This image was taken at a distance.
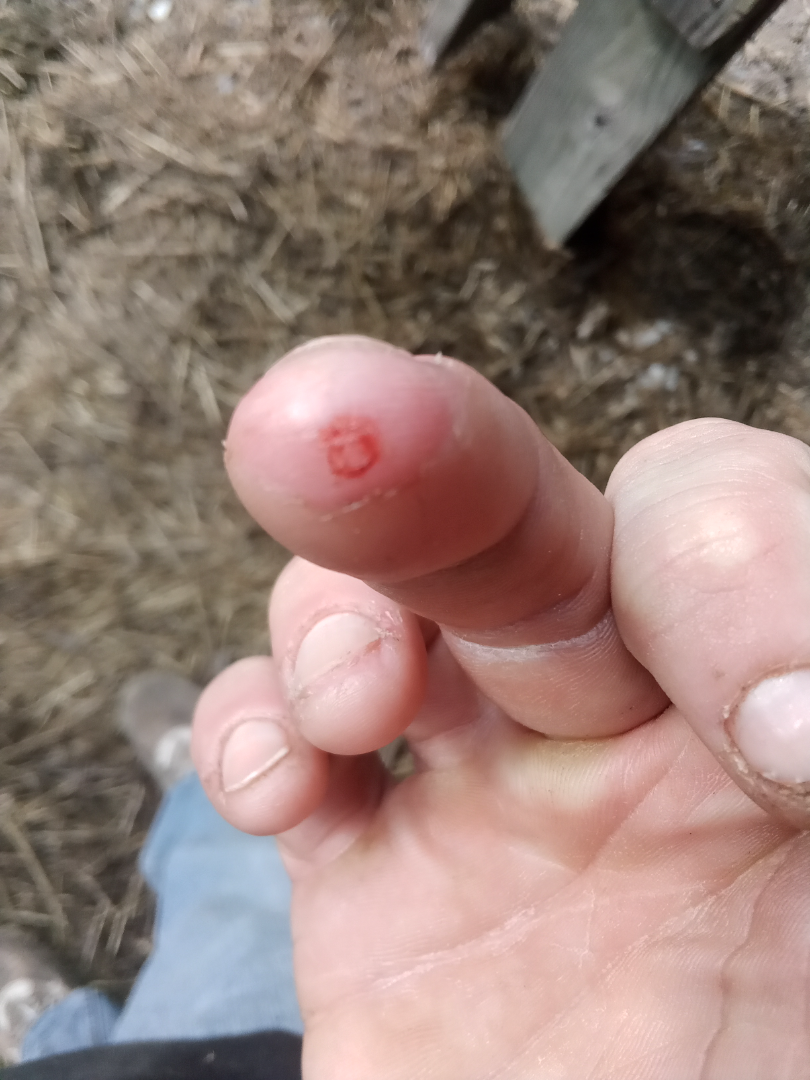* impression — one reviewing dermatologist: in keeping with Irritant Contact Dermatitis